A dermatoscopic image of a skin lesion.
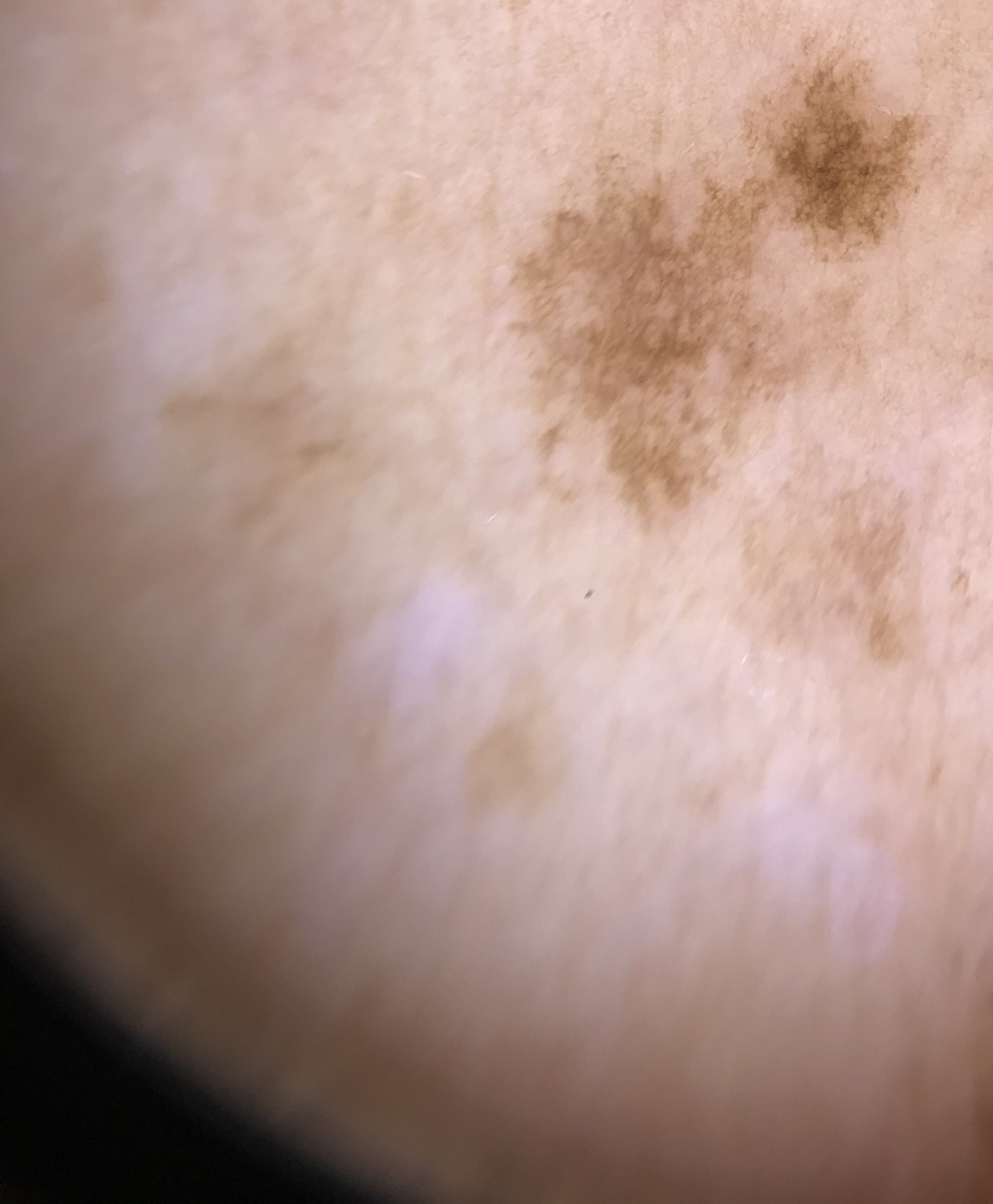The diagnosis was a solar lentigo.